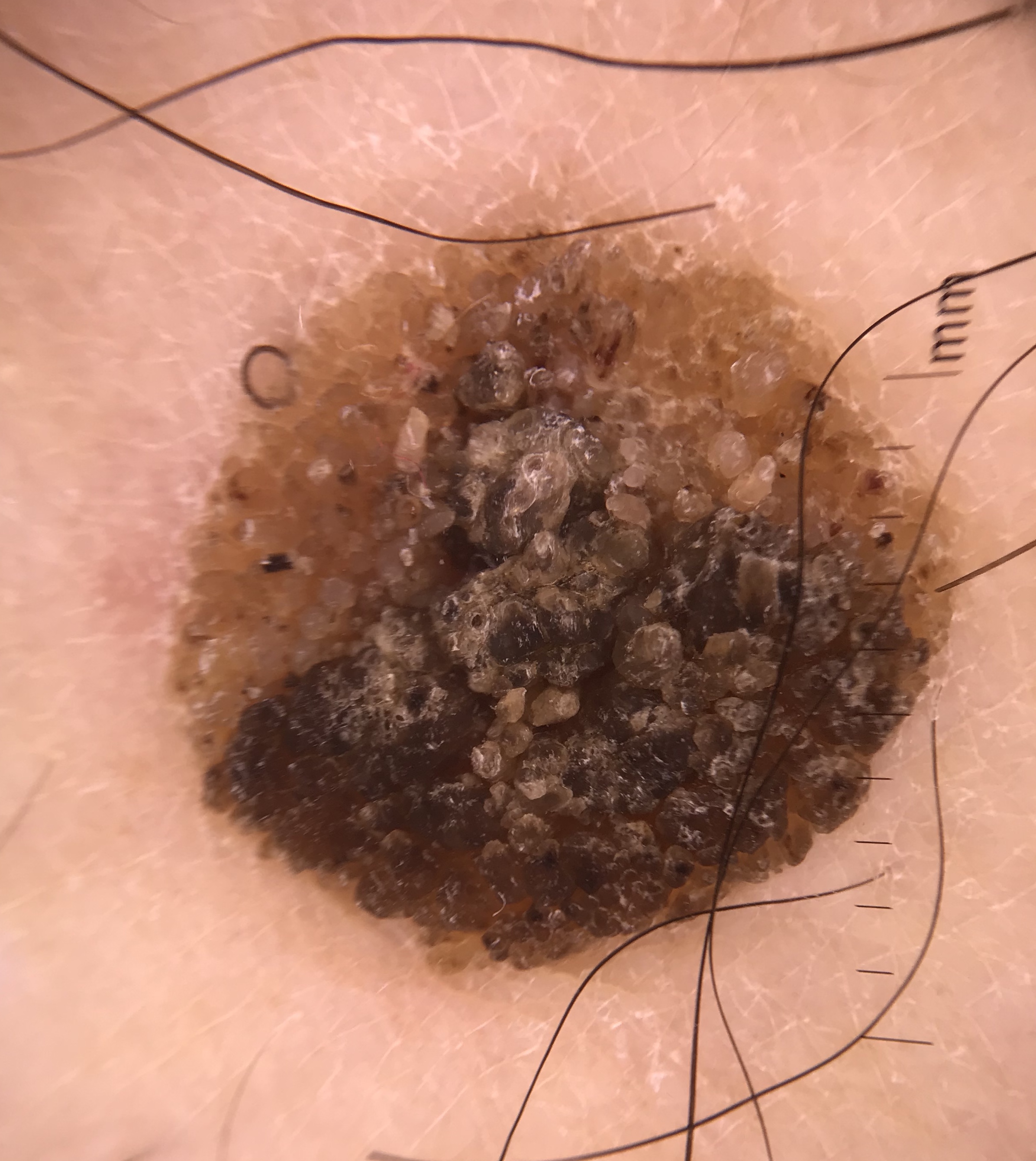Conclusion:
Diagnosed as a keratinocytic lesion — a seborrheic keratosis.